Close-up view:
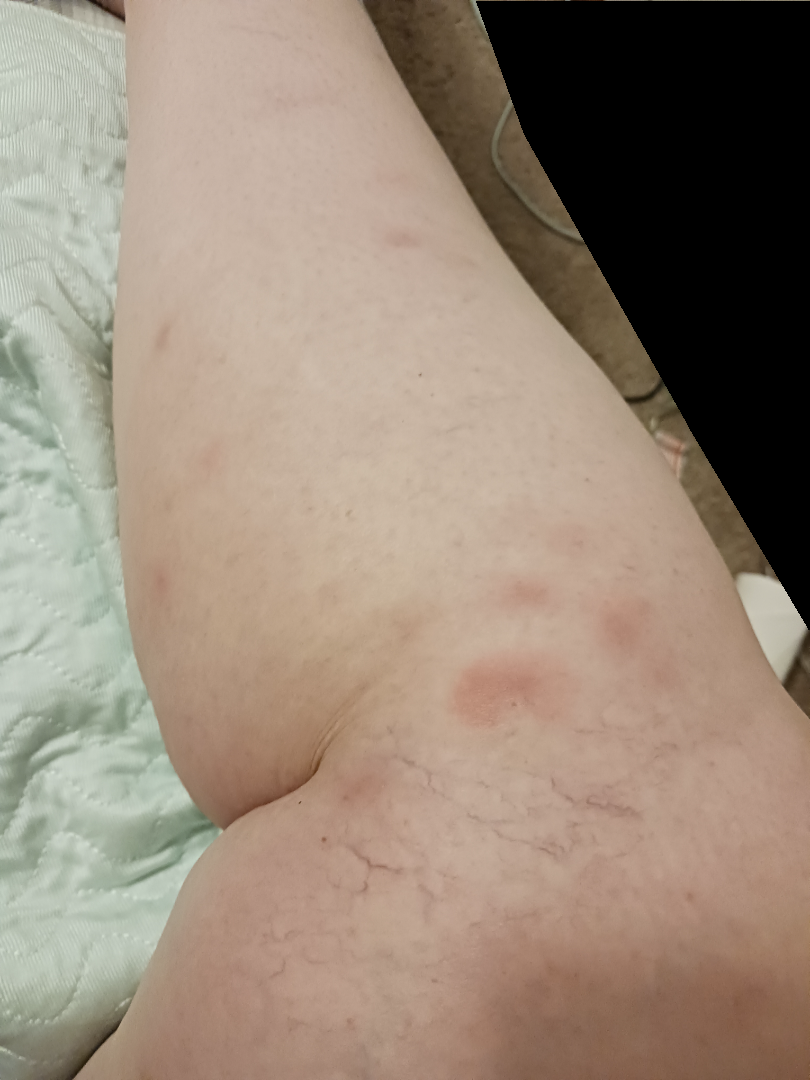differential diagnosis — the leading consideration is Erythema nodosum; also consider Panniculitis, NOS; less probable is Insect Bite.